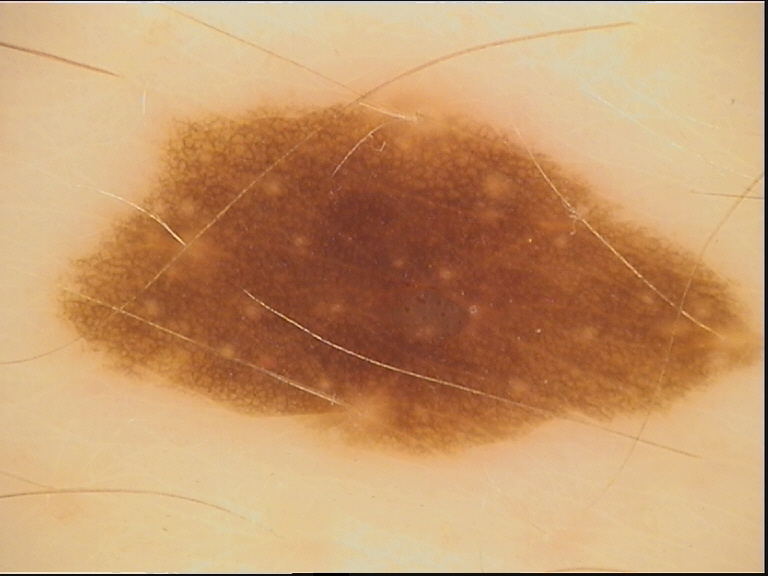Labeled as a dysplastic junctional nevus.